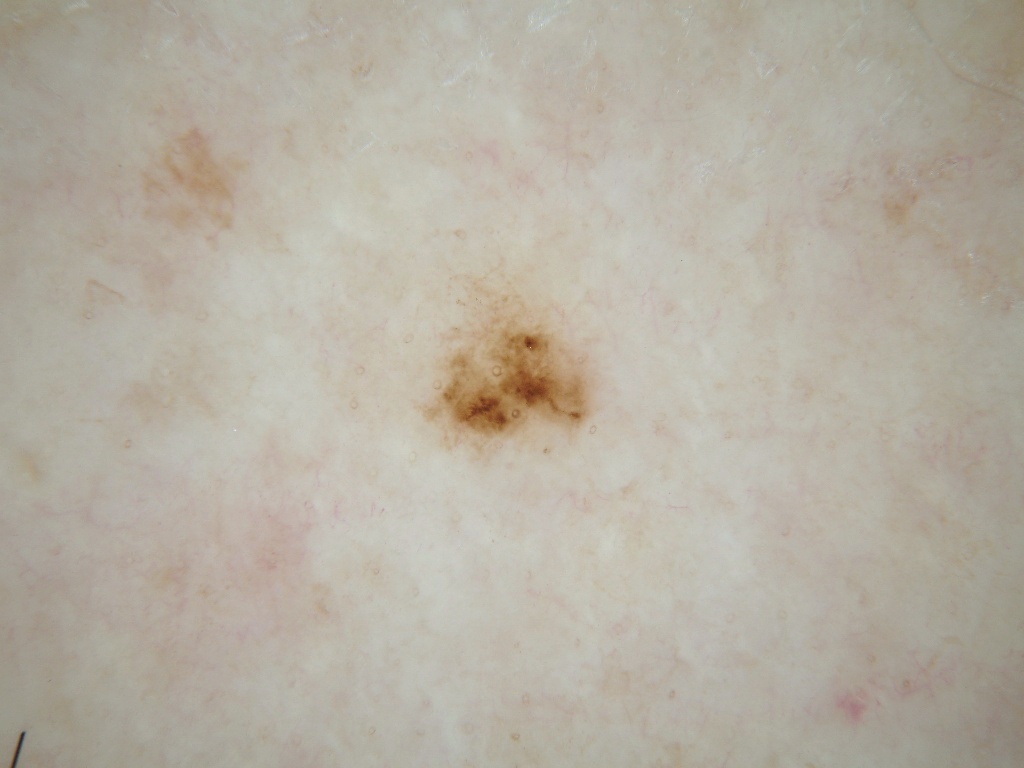Notes:
– image type — dermoscopy of a skin lesion
– lesion size — ~3% of the field
– lesion location — (415, 268, 599, 459)
– absent dermoscopic findings — pigment network, streaks, globules, negative network, and milia-like cysts
– assessment — a melanoma, a skin cancer